Dermoscopy of a skin lesion: 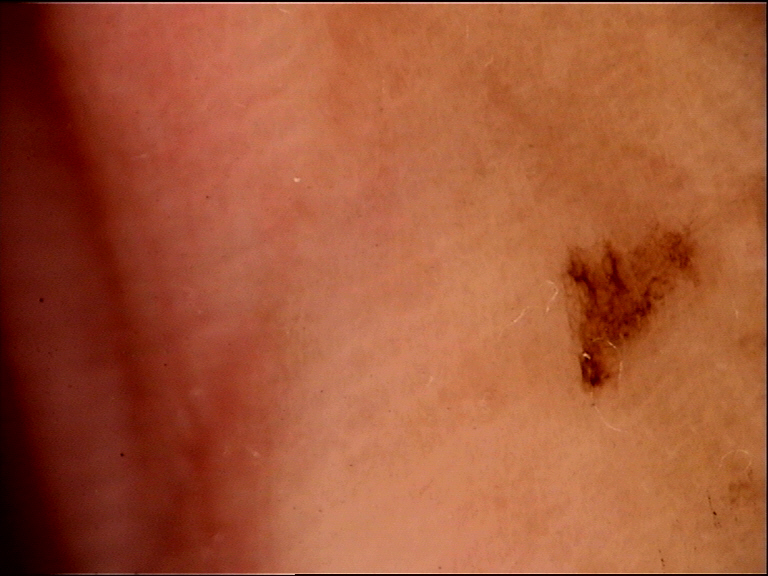Impression: Classified as a benign lesion — an acral dysplastic junctional nevus.